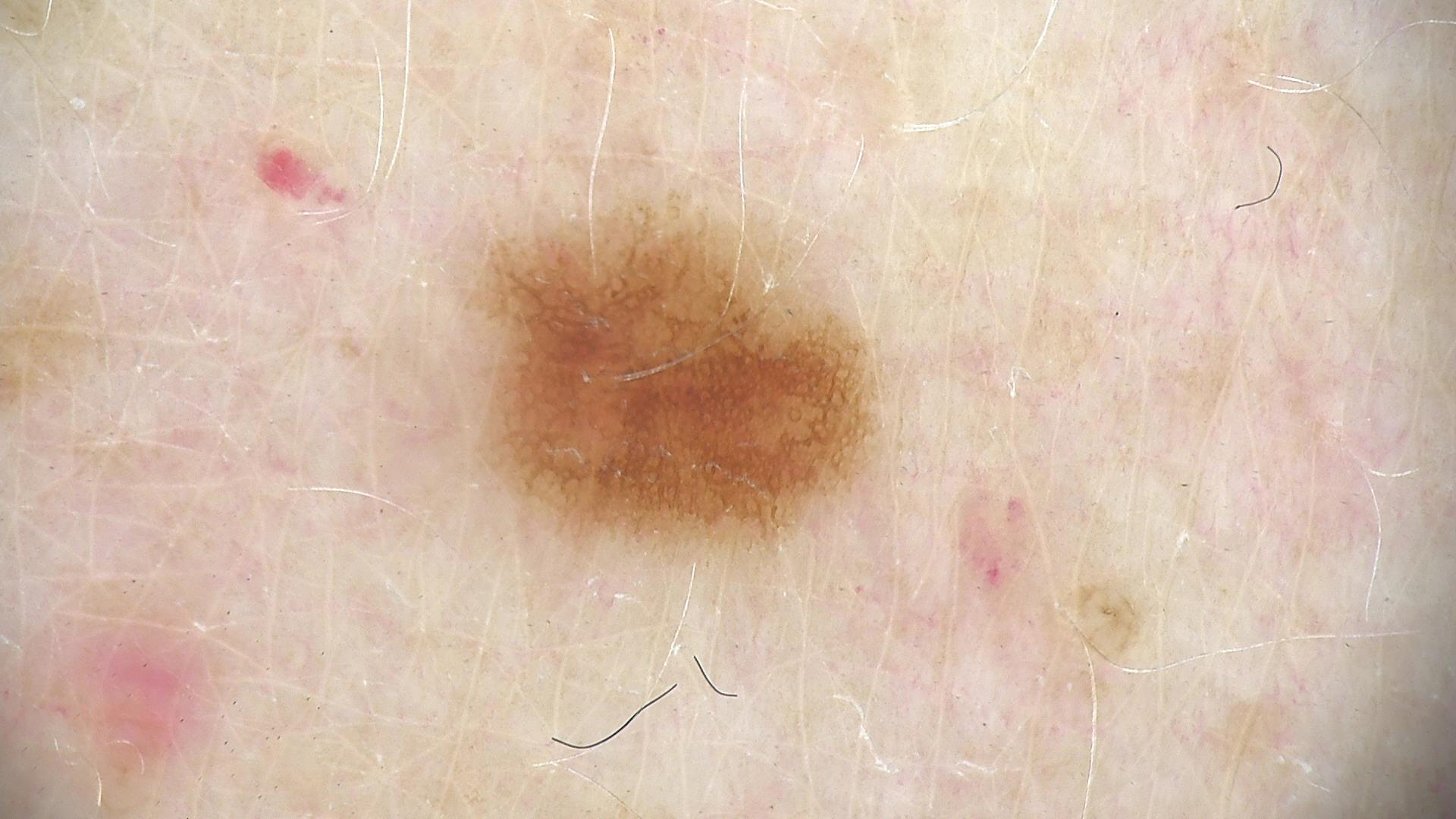A skin lesion imaged with a dermatoscope.
The diagnostic label was a dysplastic junctional nevus.